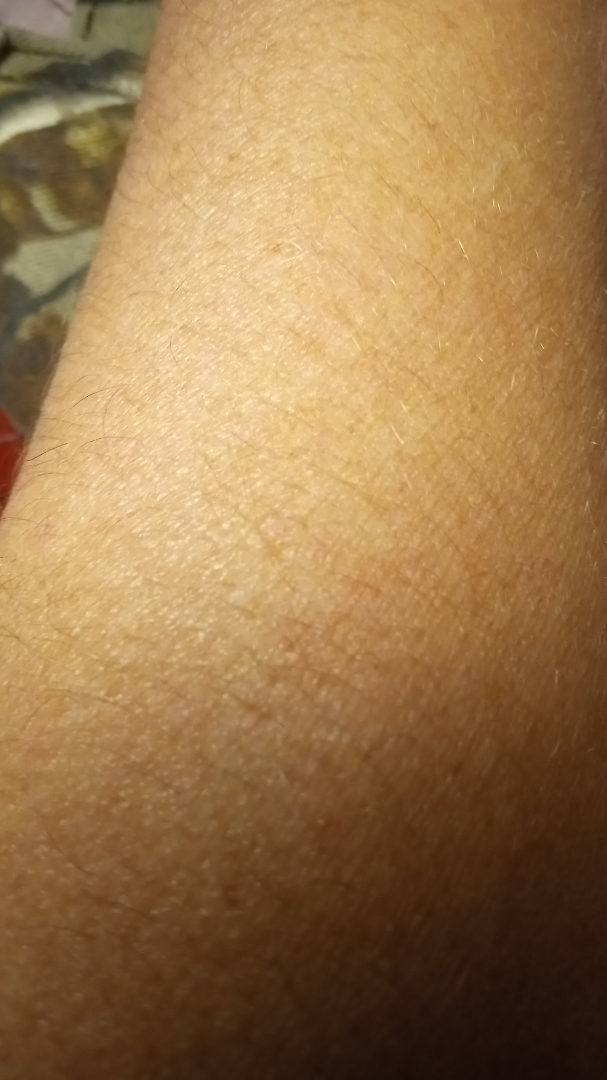No discernible pathology was noted by the reviewing dermatologist.
The patient notes bothersome appearance and itching.
Self-categorized by the patient as a rash.
The patient is 40–49, female.
No relevant systemic symptoms.
A close-up photograph.
The condition has been present for about one day.